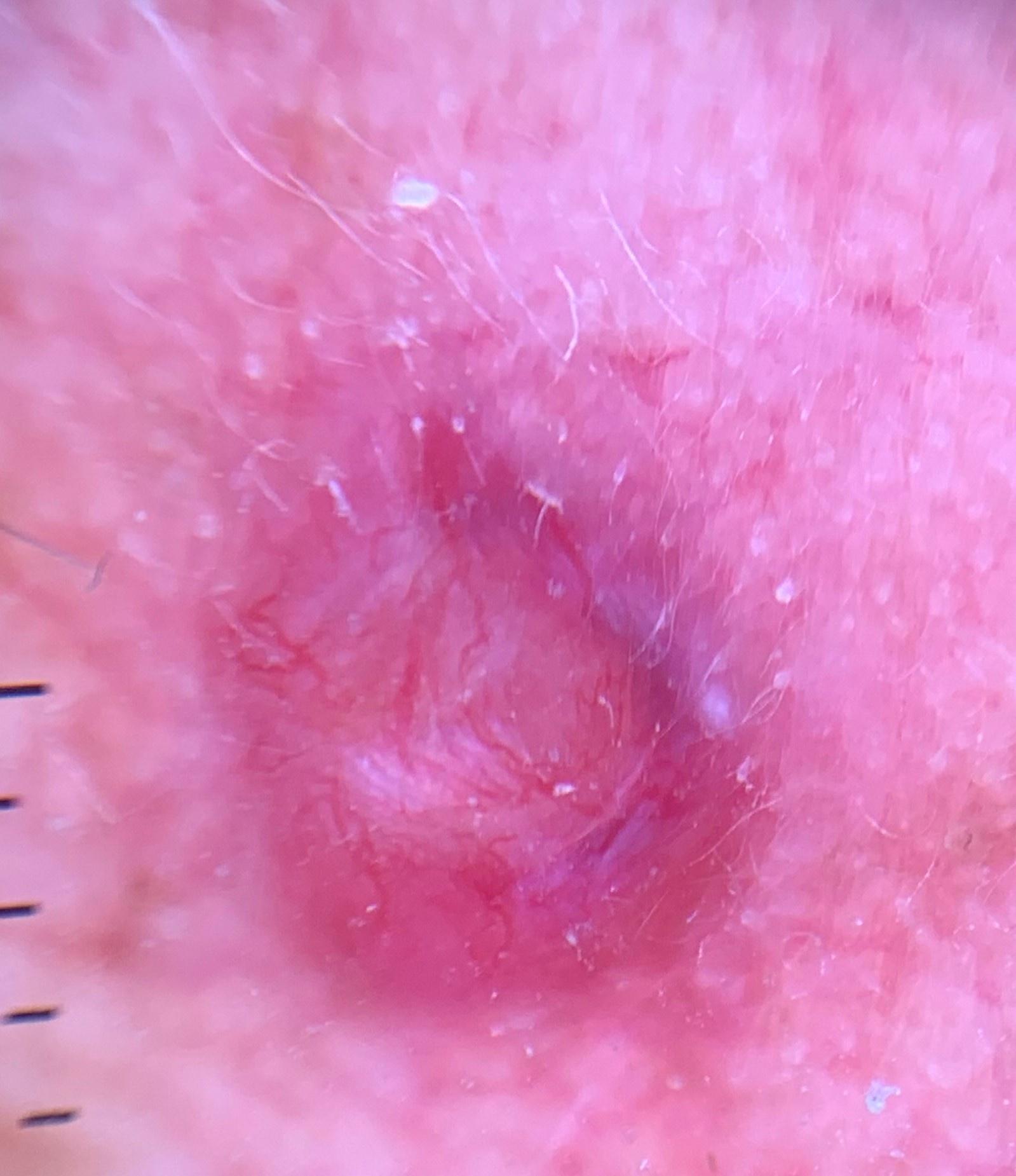| feature | finding |
|---|---|
| subject | male, aged approximately 70 |
| imaging | contact-polarized dermoscopy |
| diagnostic label | Basal cell carcinoma (biopsy-proven) |